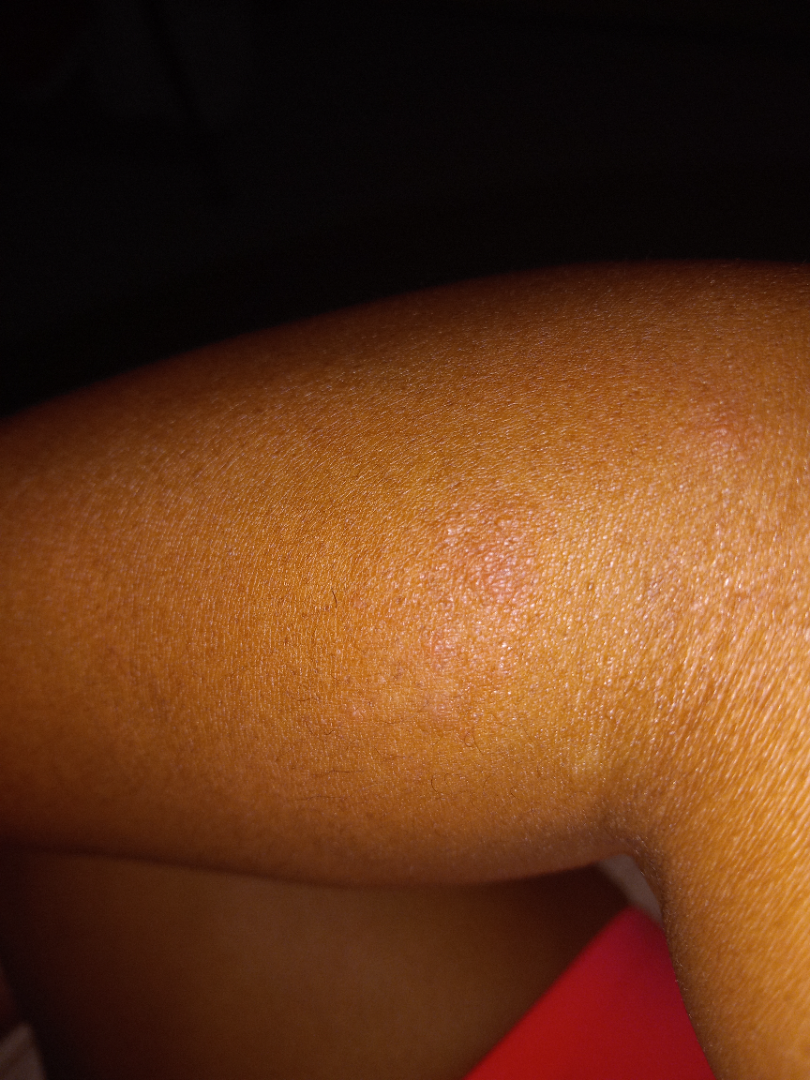The patient considered this a rash. The photograph is a close-up of the affected area. The contributor notes the lesion is raised or bumpy. The contributor notes itching. The affected area is the arm. The contributor notes the condition has been present for one to four weeks. Most likely Eczema; possibly Psoriasis.